A dermoscopy image of a single skin lesion · a male subject, approximately 15 years of age: 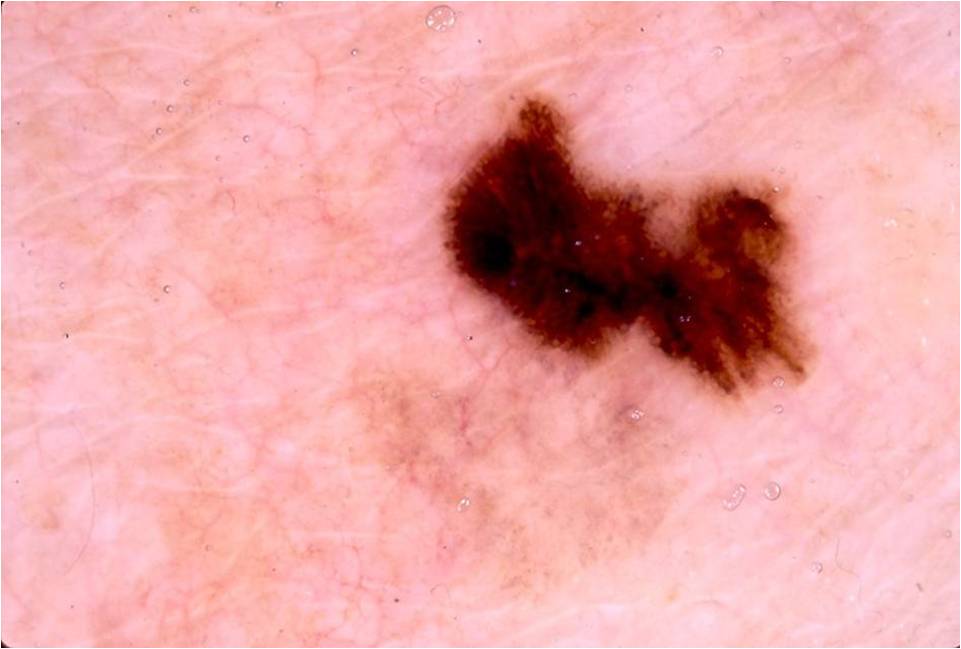Image and clinical context: The lesion is bounded by 436, 94, 803, 393. Dermoscopy demonstrates streaks, globules, and pigment network, with no milia-like cysts or negative network. Conclusion: The biopsy diagnosis was a melanoma.